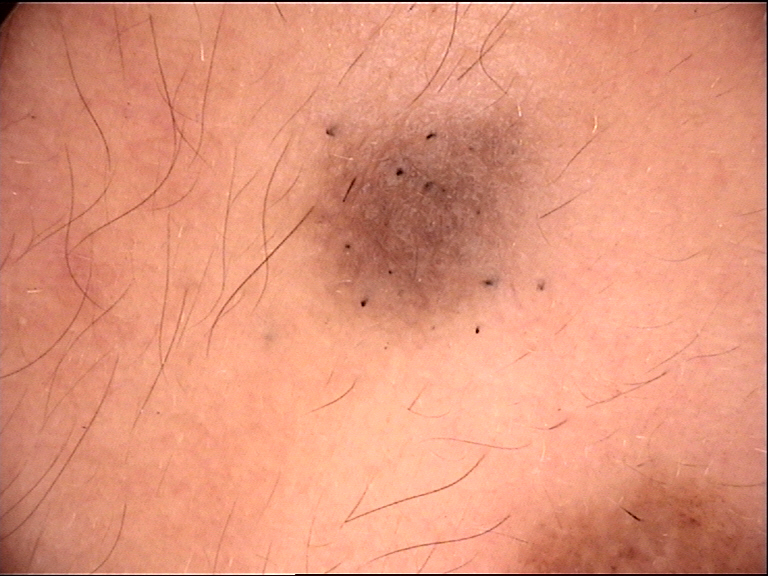Q: What is the diagnosis?
A: compound nevus (expert consensus)